The contributor is a female aged 40–49, close-up view, the lesion is described as fluid-filled, self-categorized by the patient as a rash, the condition has been present for about one day, no associated systemic symptoms reported, the lesion is associated with bothersome appearance and darkening — 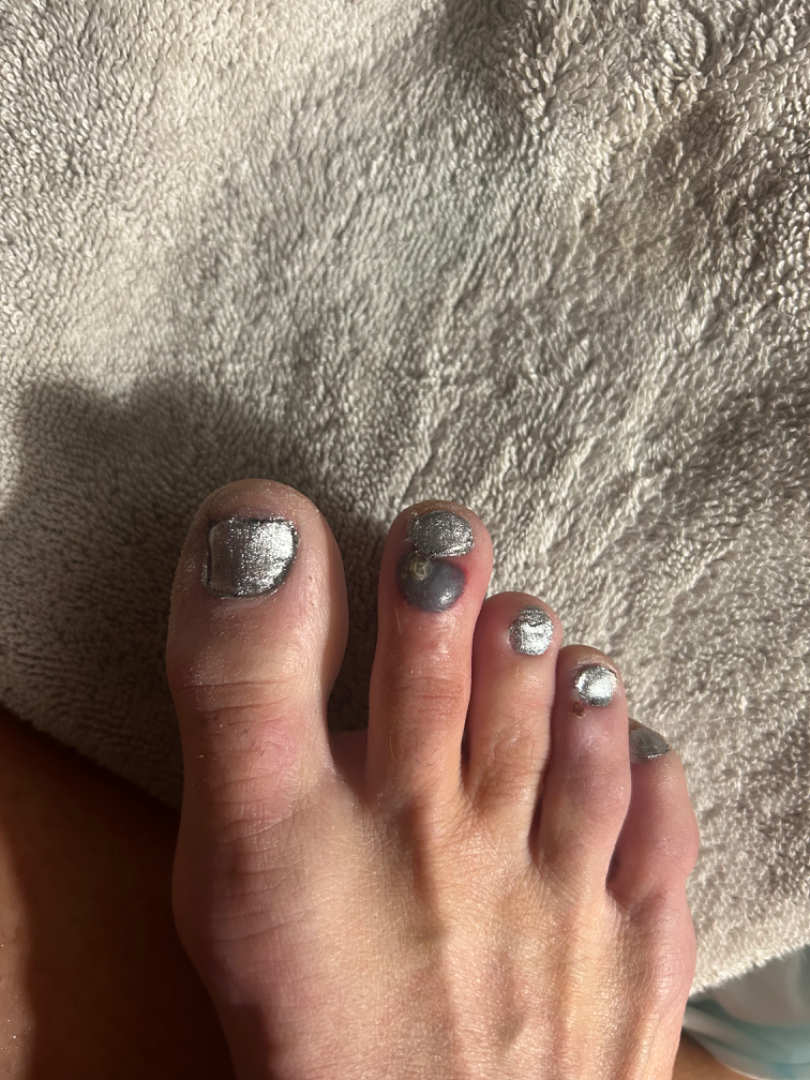Case summary:
– assessment · the impression was split between Hematoma of skin and Blood blister; a remote consideration is Angiokeratoma of skin; less probable is Melanoma